The photograph was taken at a distance. Located on the arm. The condition has been present for about one day:
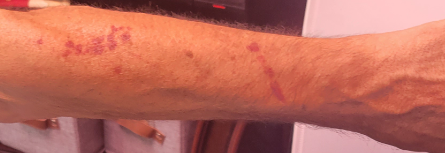Single-reviewer assessment: most consistent with ecchymoses.